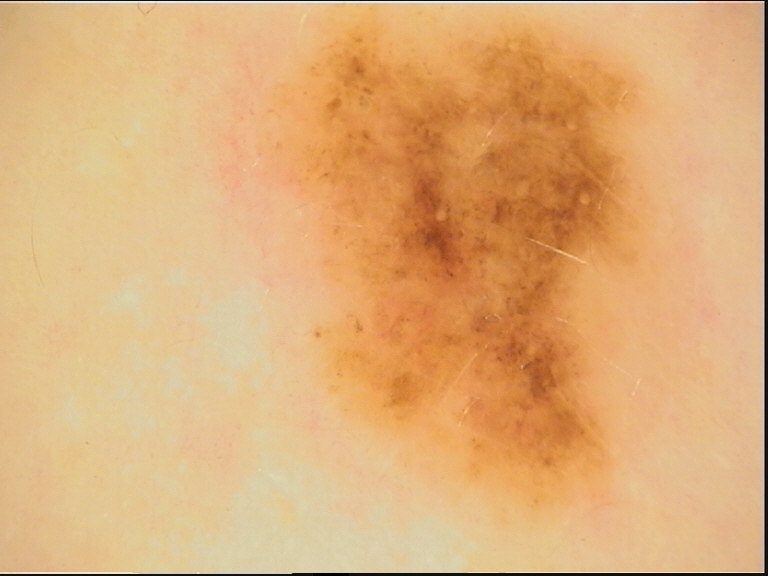Findings:
- imaging · dermatoscopy
- class · dysplastic junctional nevus (expert consensus)